Skin tone: Fitzpatrick I; the lesion involves the arm; this is a close-up image; the patient described the issue as a rash; the subject is 40–49, female; present for less than one week.
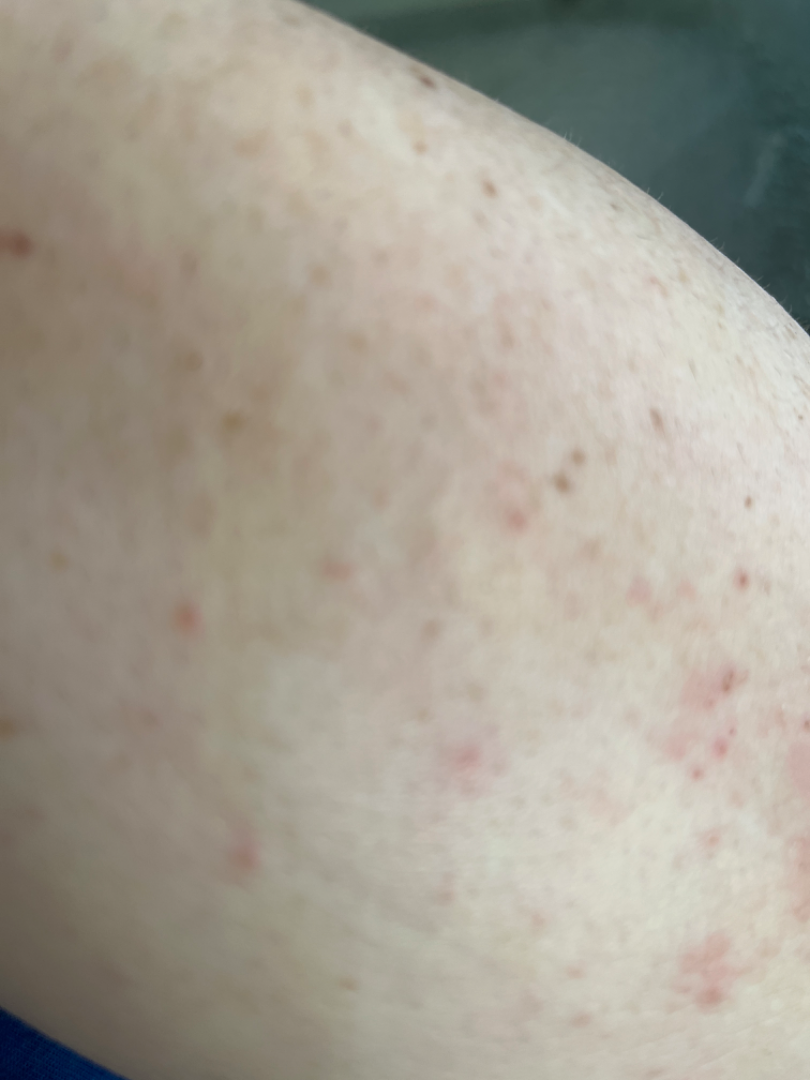| feature | finding |
|---|---|
| assessment | favoring Acne; also on the differential is Eczema; also raised was Allergic Contact Dermatitis |